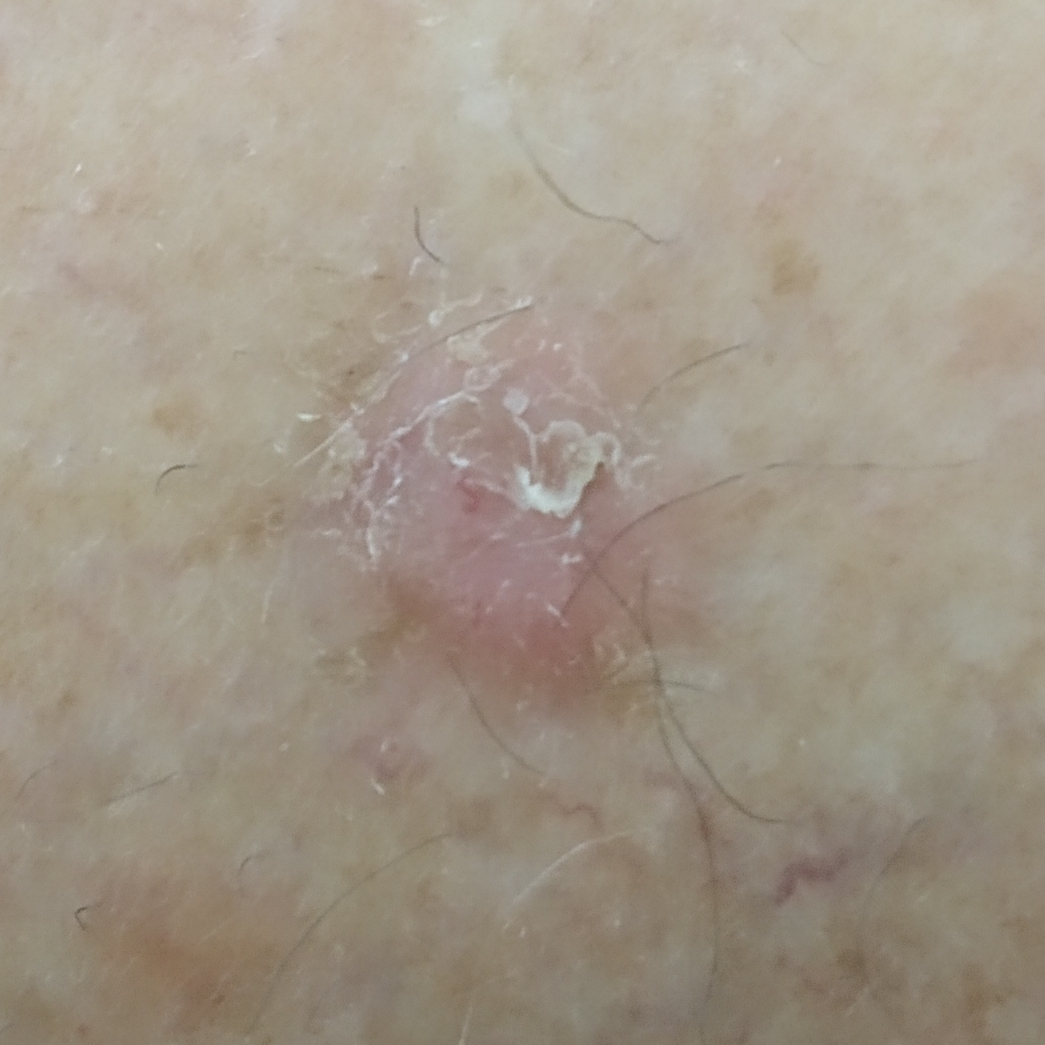Notes:
* diagnosis — basal cell carcinoma (biopsy-proven)